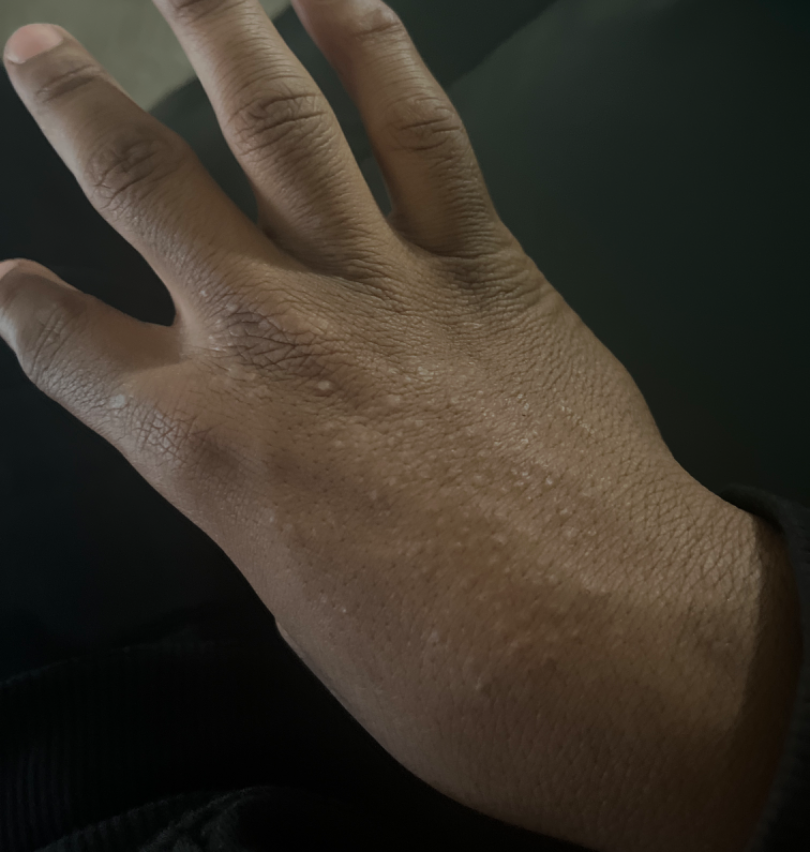Review:
The condition could not be reliably identified from the image.